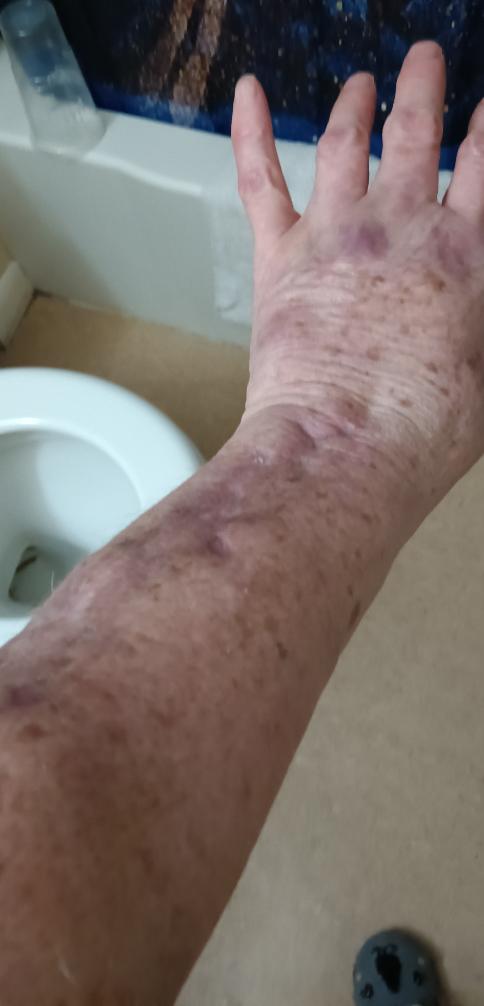assessment: unable to determine.